Close-up view. The lesion involves the leg. The condition has been present for one to four weeks. The lesion is described as raised or bumpy:
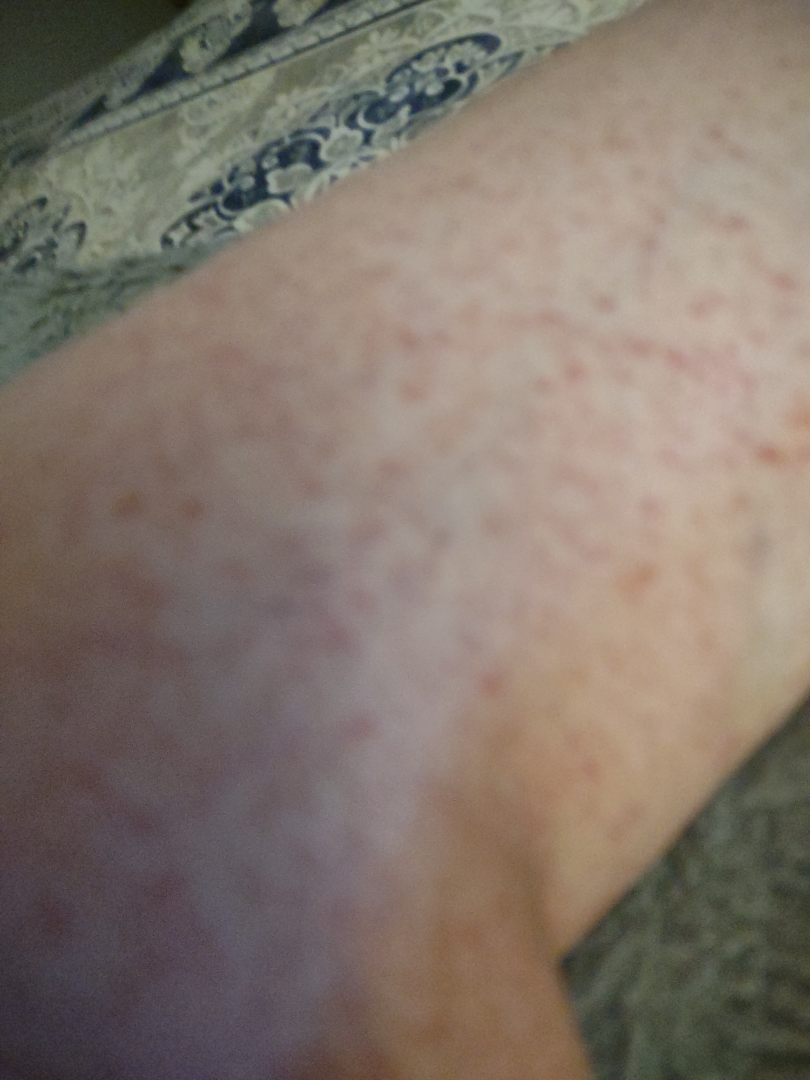Notes:
- assessment — indeterminate from the photograph